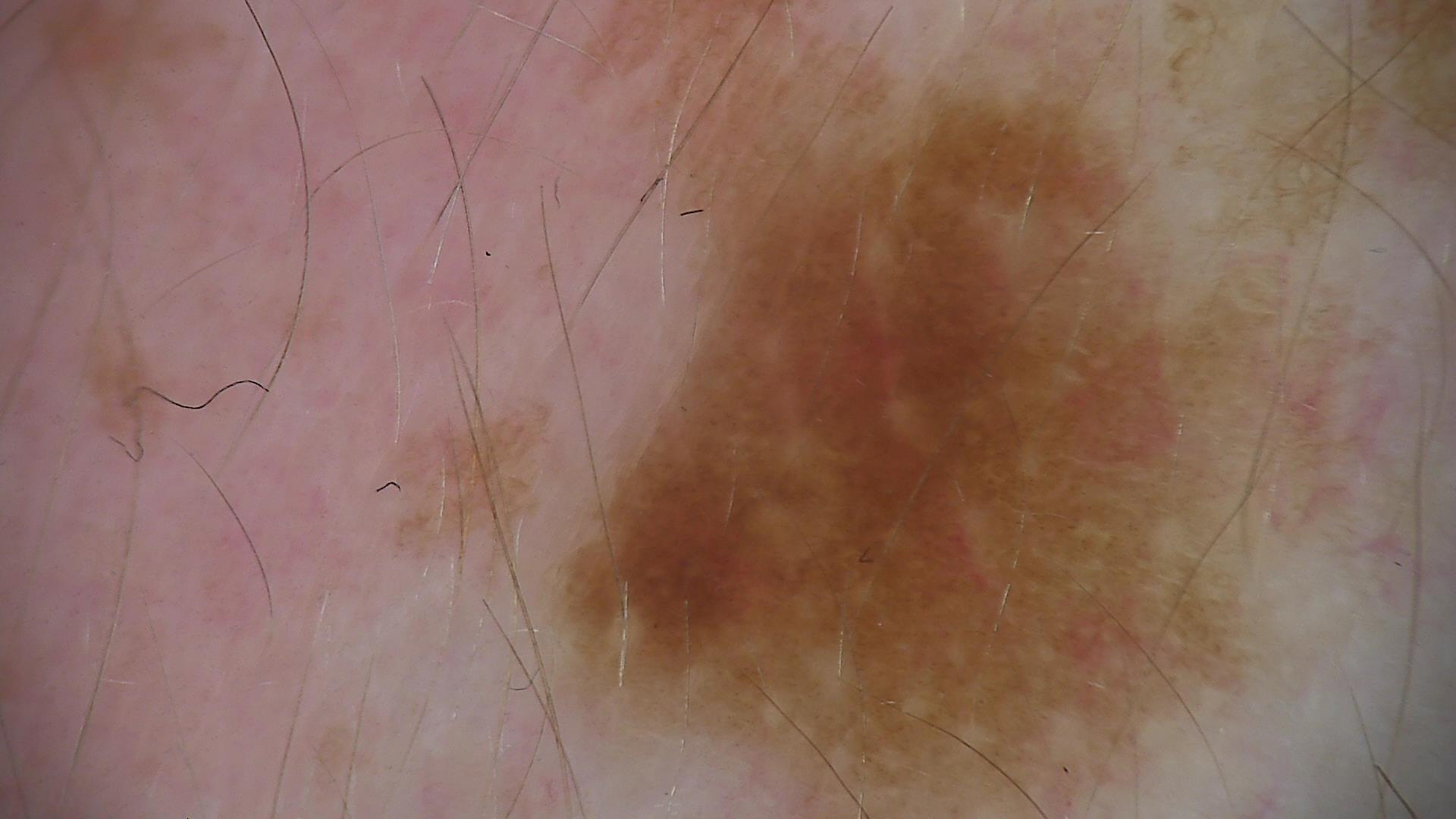Classified as a seborrheic keratosis.